A male patient aged 78-82 · this is a dermoscopic photograph of a skin lesion:
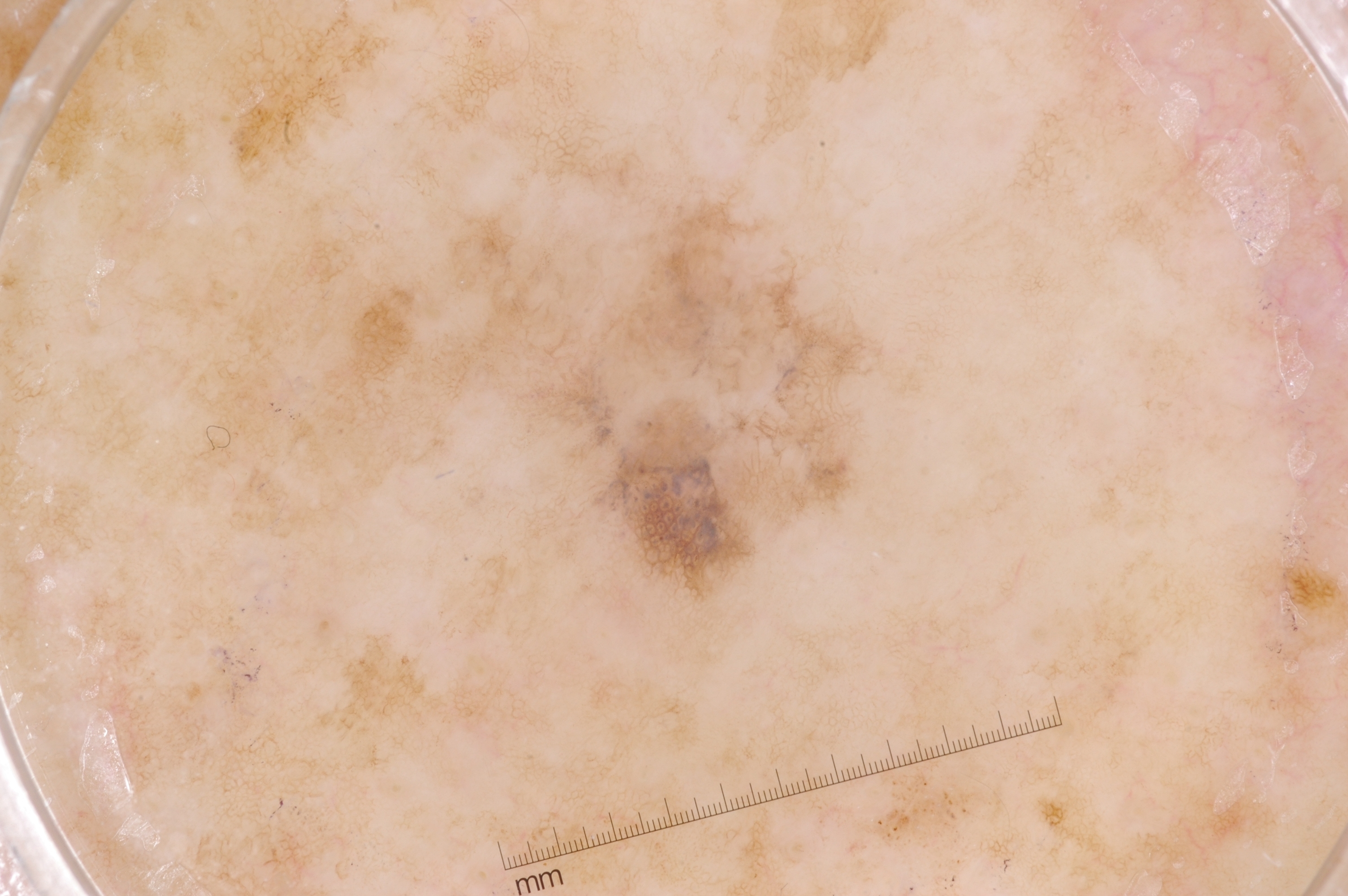With coordinates (x1, y1, x2, y2), the lesion's extent is [521, 173, 894, 631].
Dermoscopically, the lesion shows pigment network and milia-like cysts.
On biopsy, the diagnosis was a melanoma.